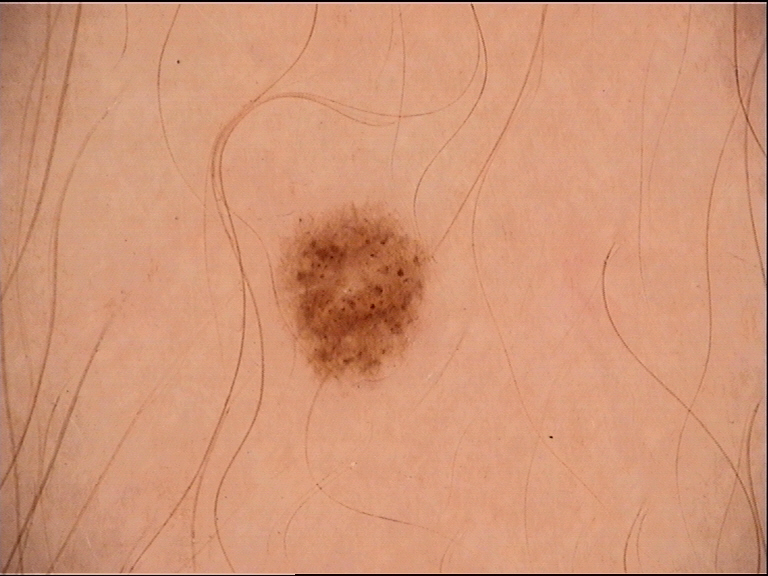Case:
- image type: dermoscopy
- label: dysplastic junctional nevus (expert consensus)